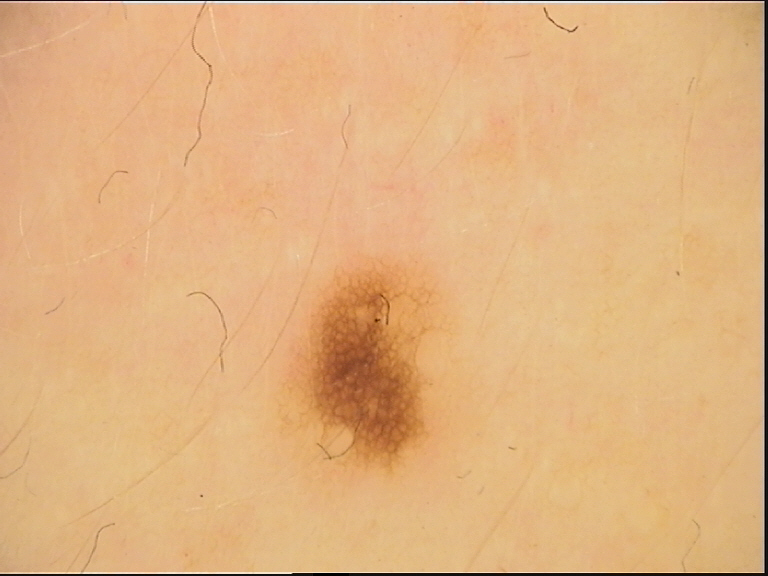This is a banal lesion. The diagnosis was a junctional nevus.